Dermoscopy of a skin lesion.
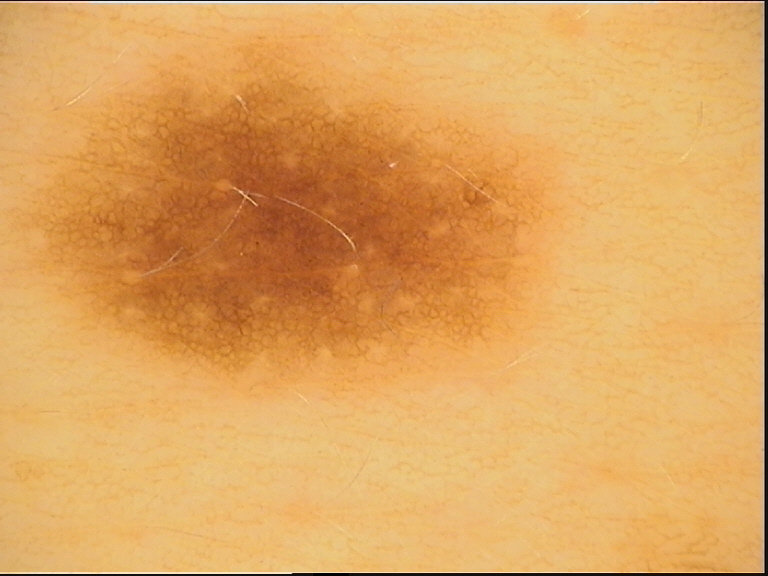This is a banal lesion. The diagnostic label was a junctional nevus.